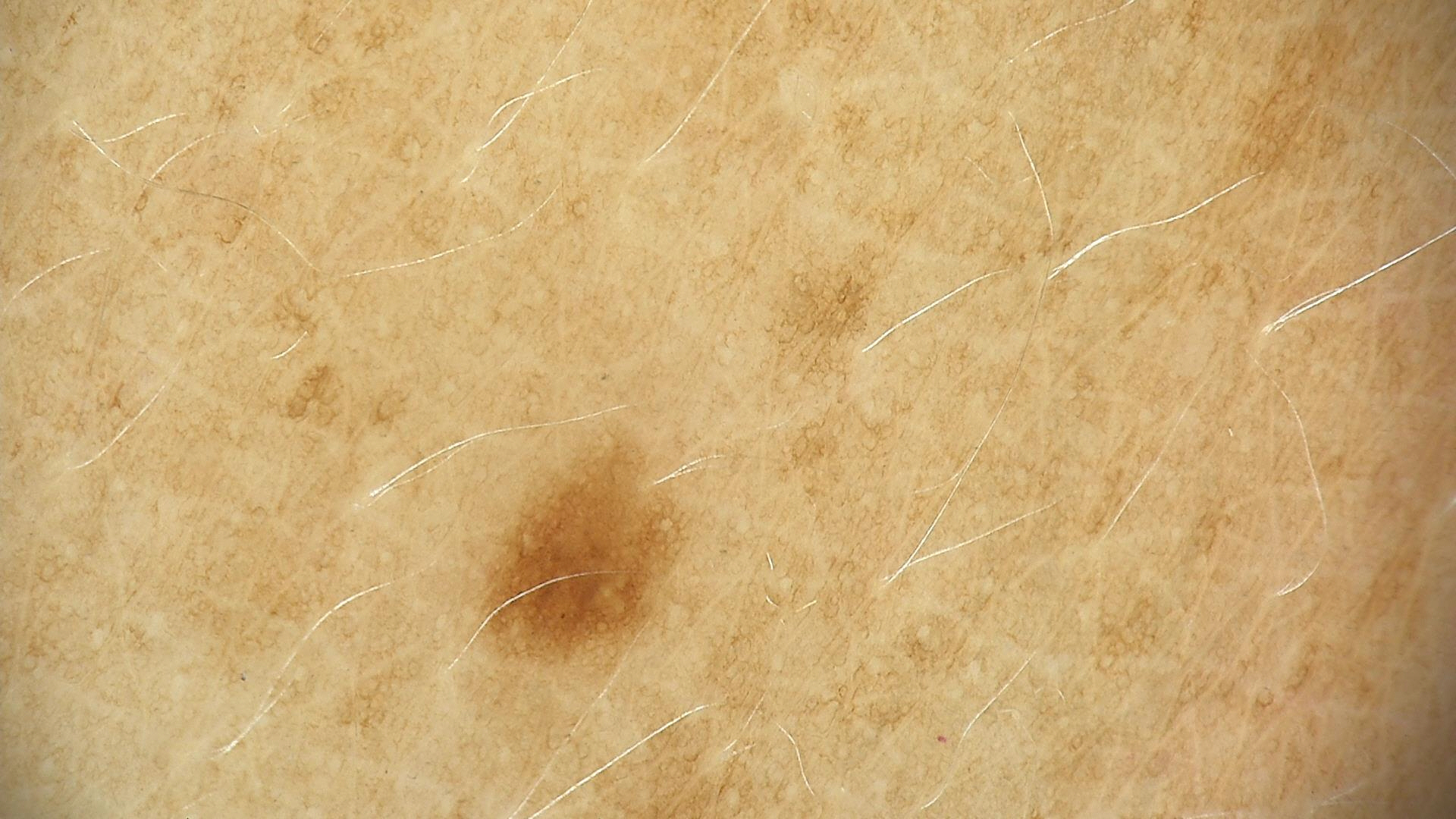Conclusion: The diagnosis was a dysplastic junctional nevus.